A clinical close-up photograph of a skin lesion; a subject 31 years of age.
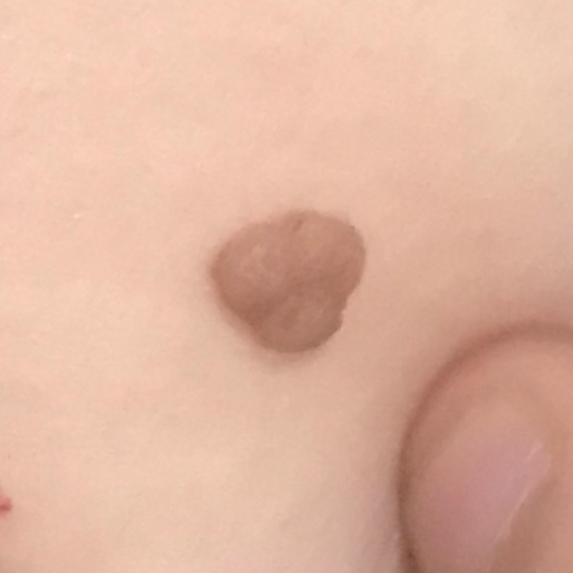Impression:
Consistent with a benign skin lesion — a nevus.